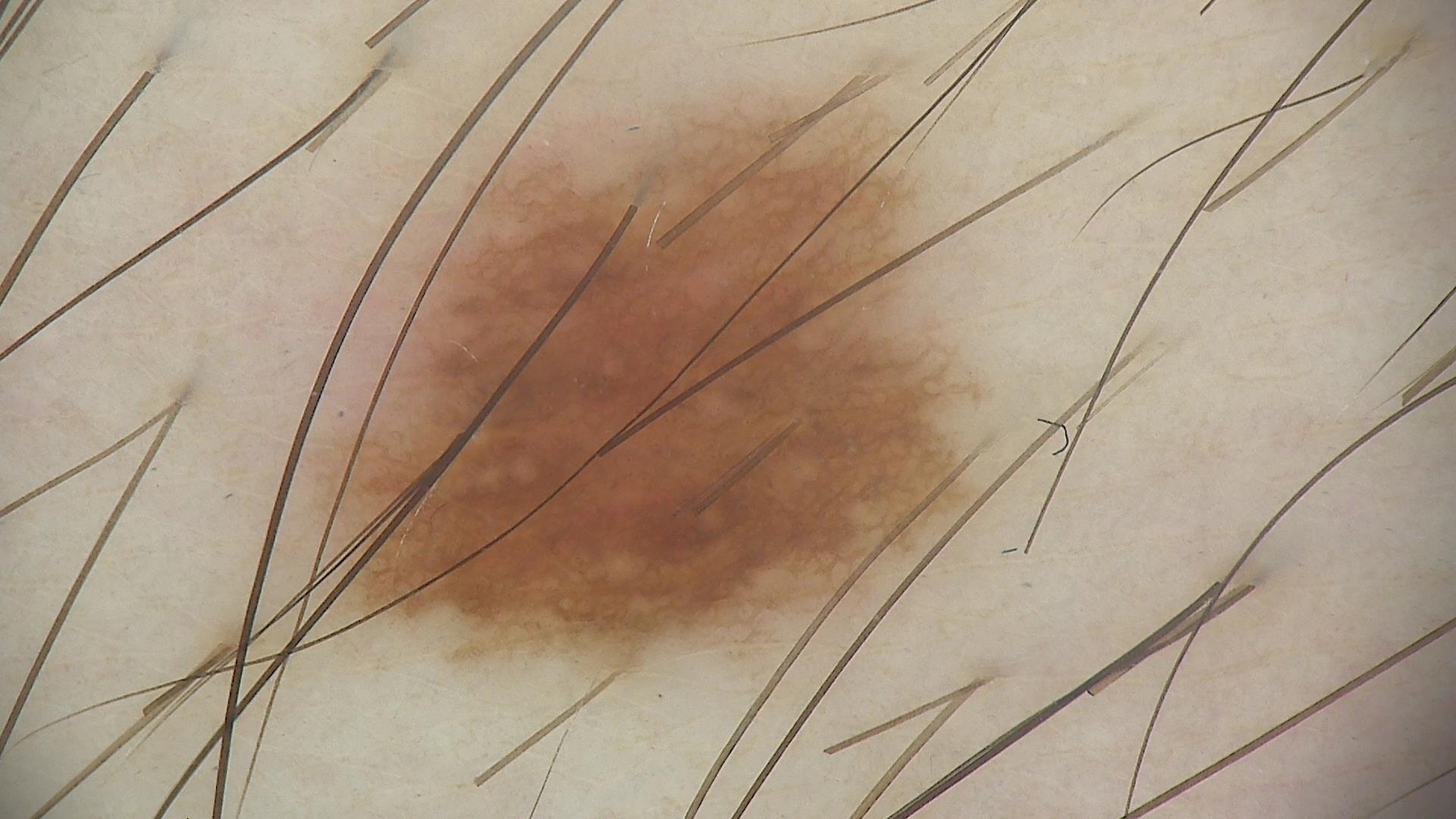| field | value |
|---|---|
| modality | dermoscopy |
| class | dysplastic junctional nevus (expert consensus) |